A dermatoscopic image of a skin lesion.
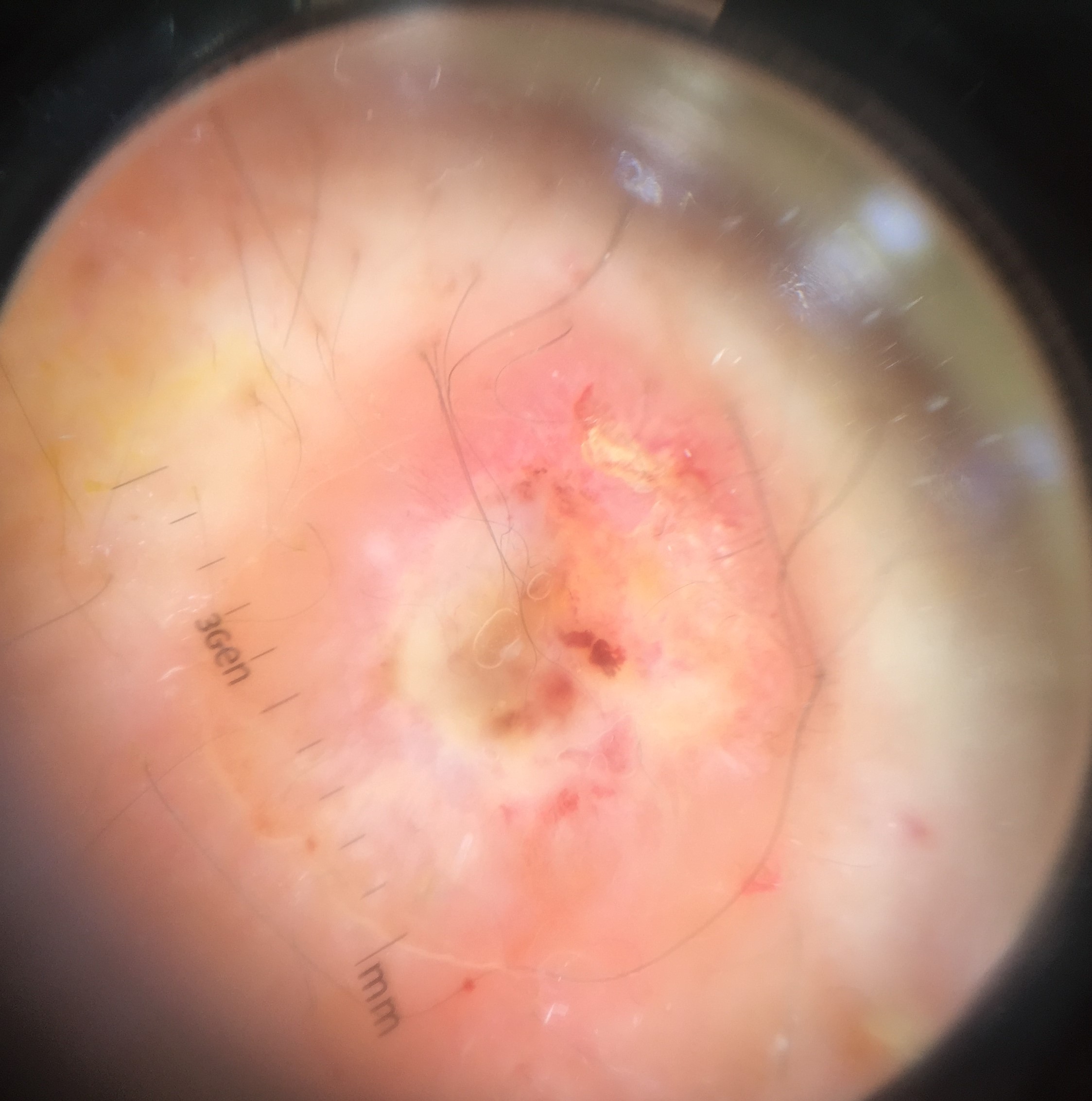{"diagnosis": {"name": "squamous cell carcinoma", "code": "scc", "malignancy": "malignant", "super_class": "non-melanocytic", "confirmation": "histopathology"}}